A dermoscopy image of a single skin lesion.
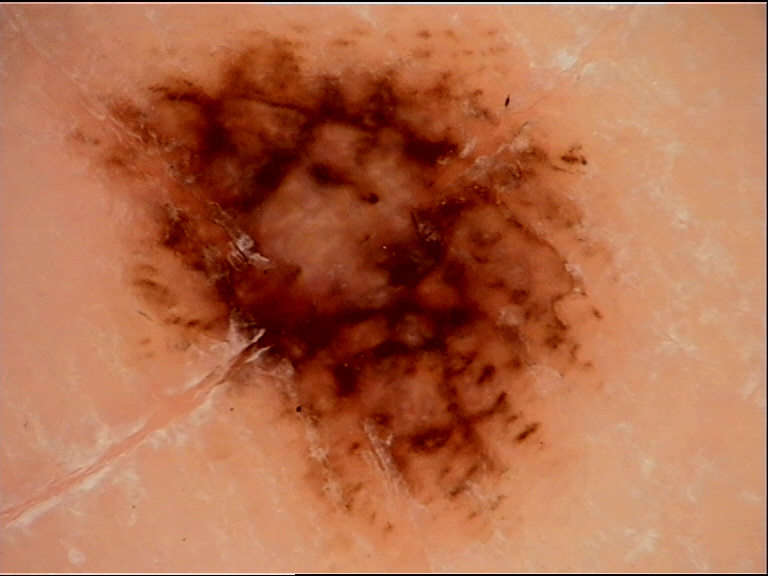Histopathologically confirmed as a malignancy — an acral lentiginous melanoma.